An image taken at an angle; located on the arm:
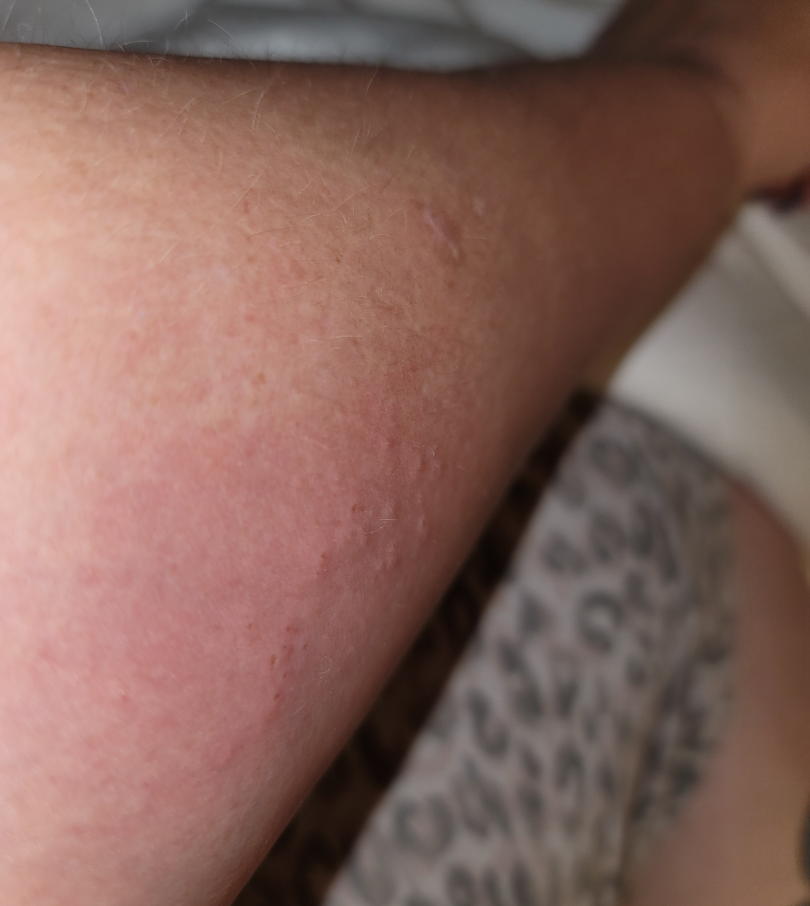Review: The case was indeterminate on photographic review.